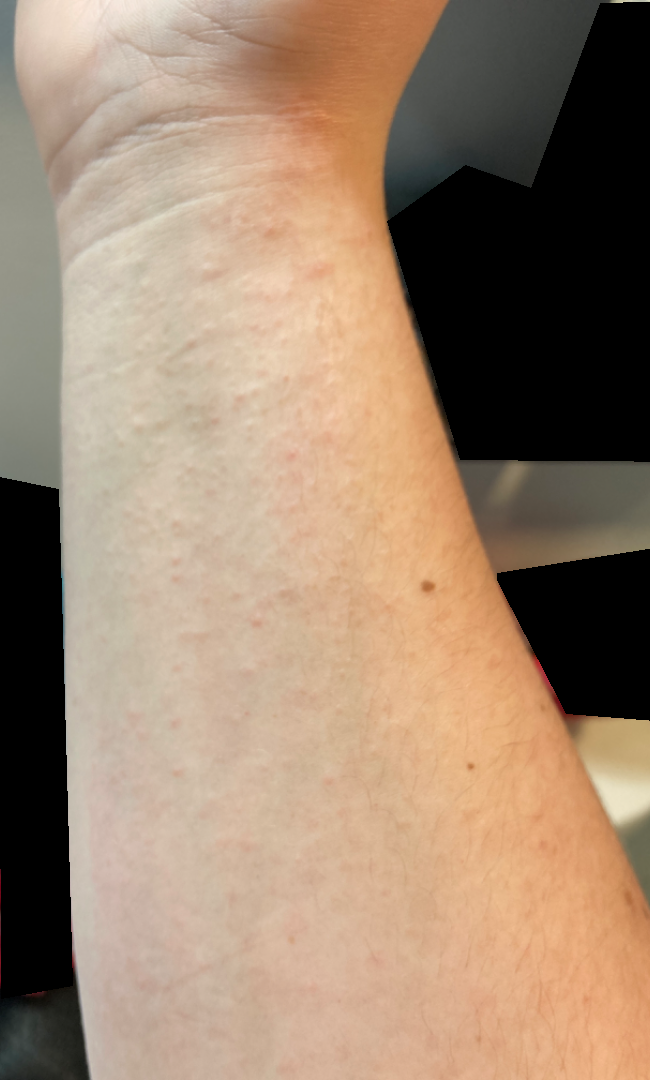Impression: On teledermatology review: most consistent with Eczema.